A patient 10 years old; a clinical photograph showing a skin lesion:
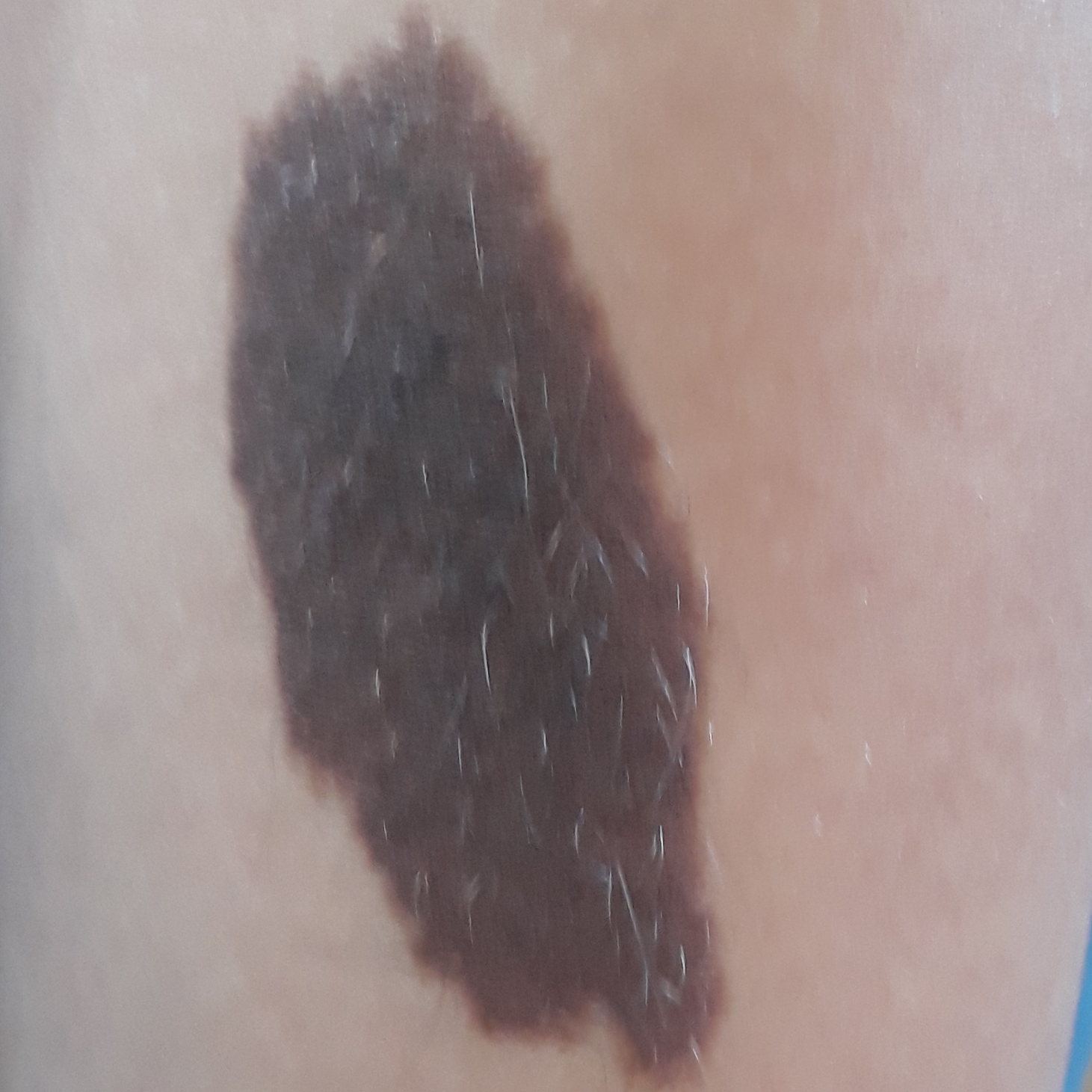Q: What is the anatomic site?
A: a forearm
Q: What does the patient describe?
A: growth, change in appearance / no elevation, no pain
Q: What was the clinical impression?
A: nevus (clinical consensus)